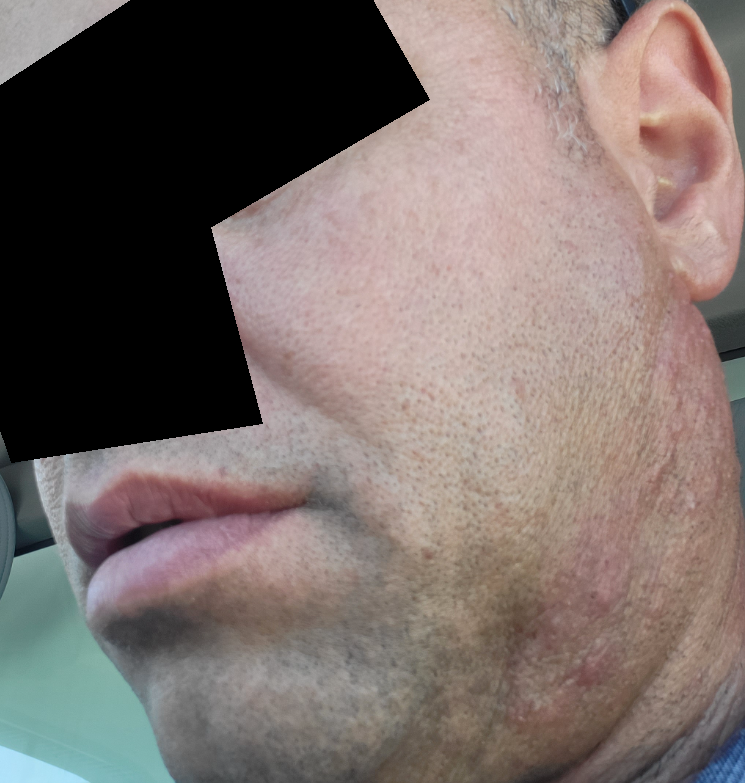dermatologist impression=three dermatologists each reviewed the case: the leading consideration is Tinea; lower on the differential is Impetigo; less probable is Allergic Contact Dermatitis; less likely is Acne; a remote consideration is Leprosy.